A dermatoscopic image of a skin lesion: 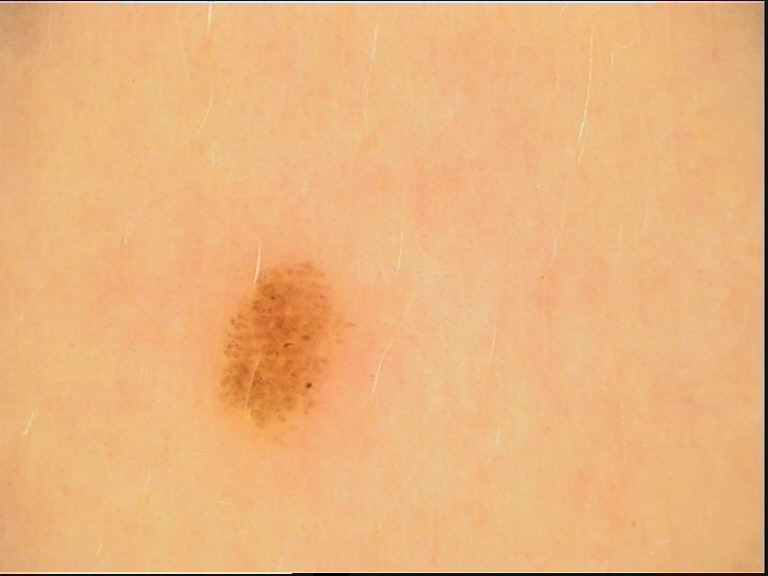diagnosis:
  name: dysplastic junctional nevus
  code: jd
  malignancy: benign
  super_class: melanocytic
  confirmation: expert consensus